The subject is a male aged 30–39; close-up view; no relevant systemic symptoms; texture is reported as fluid-filled; the patient reports the condition has been present for less than one week; the lesion is associated with bothersome appearance and itching; the lesion involves the leg.
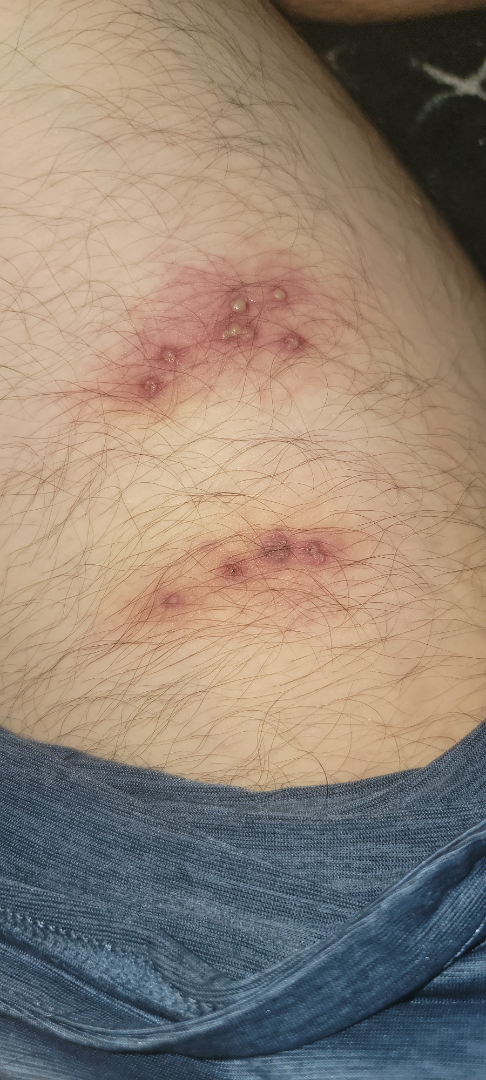The reviewing dermatologist's impression was: Herpes Zoster and Herpes Simplex were each considered, in no particular order; a more distant consideration is Impetigo.